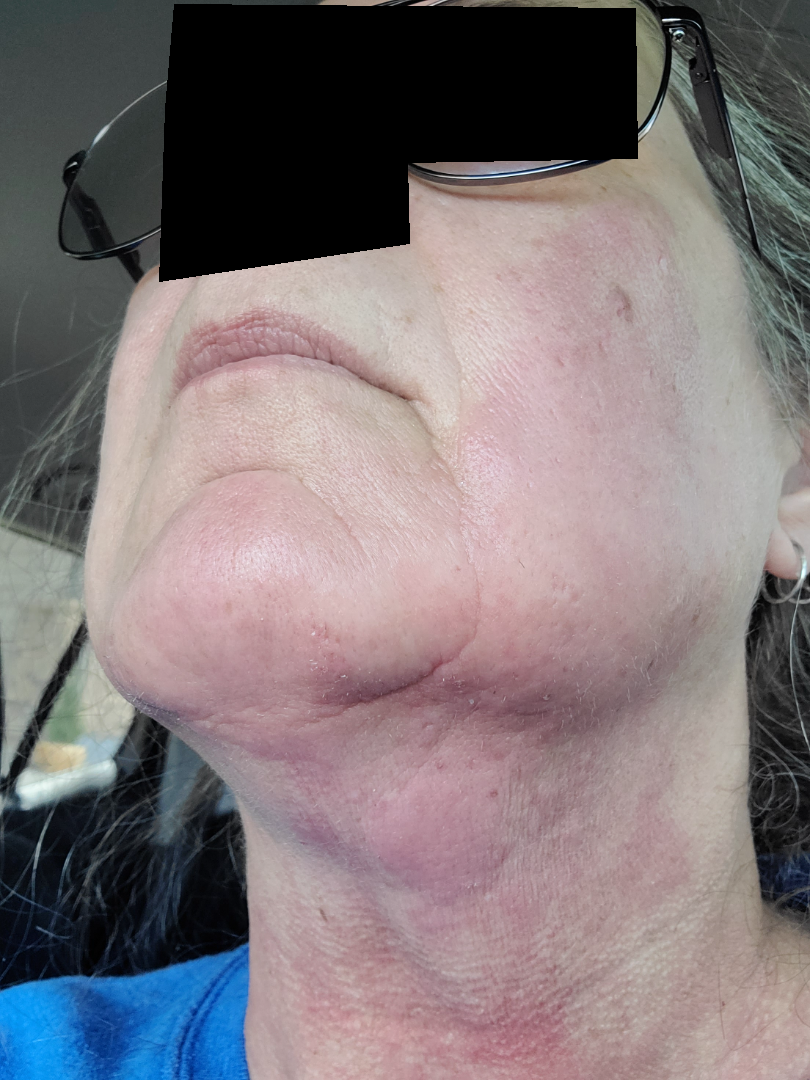Q: Image view?
A: close-up
Q: What is the affected area?
A: head or neck
Q: Age and sex?
A: female, age 60–69